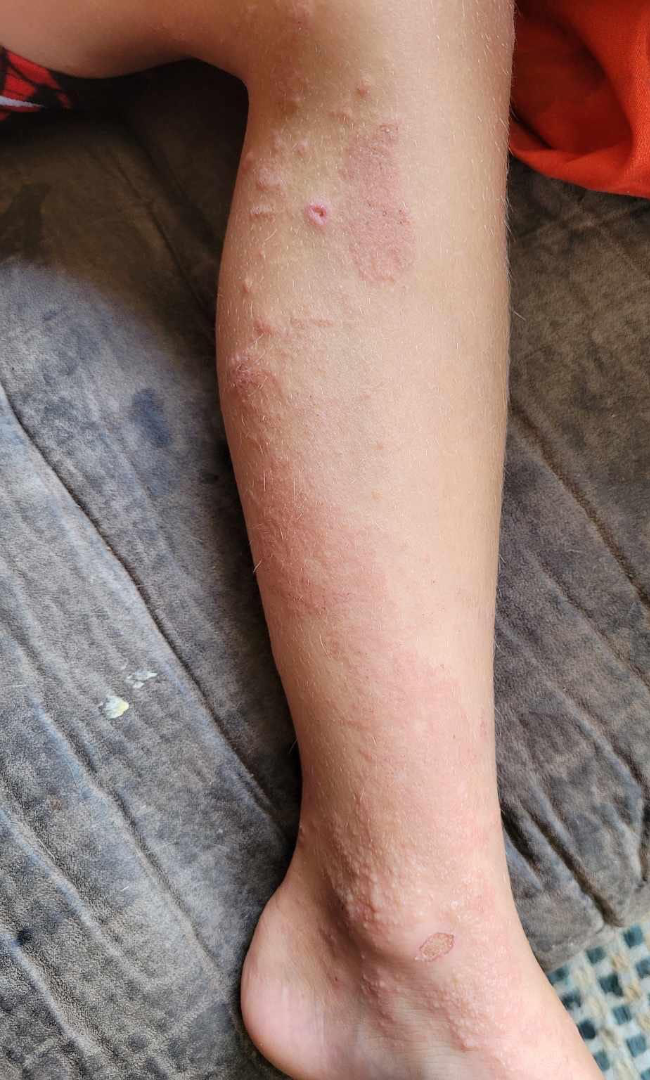{"assessment": "ungradable on photographic review", "duration": "about one day", "body_site": "leg", "shot_type": "close-up", "texture": "raised or bumpy", "systemic_symptoms": "none reported", "patient": "female, age 40–49", "patient_category": "a rash", "symptoms": "none reported"}